A clinical photograph showing a skin lesion · the chart records prior malignancy (patient or family) and prior skin cancer (patient or family) · Fitzpatrick phototype III · a female subject 63 years of age:
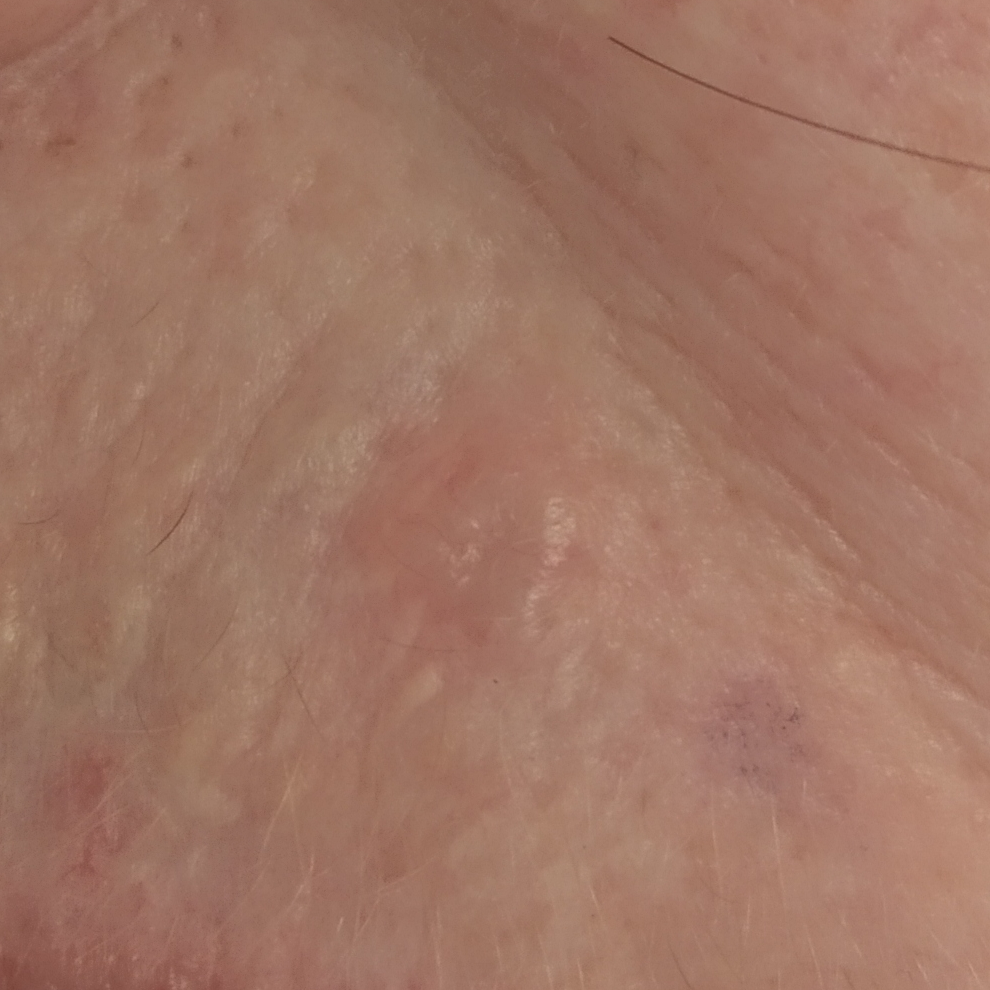The lesion is roughly 6 by 4 mm. The patient describes that the lesion is elevated and itches, but has not bled. Histopathologically confirmed as a basal cell carcinoma.